A dermoscopic photograph of a skin lesion.
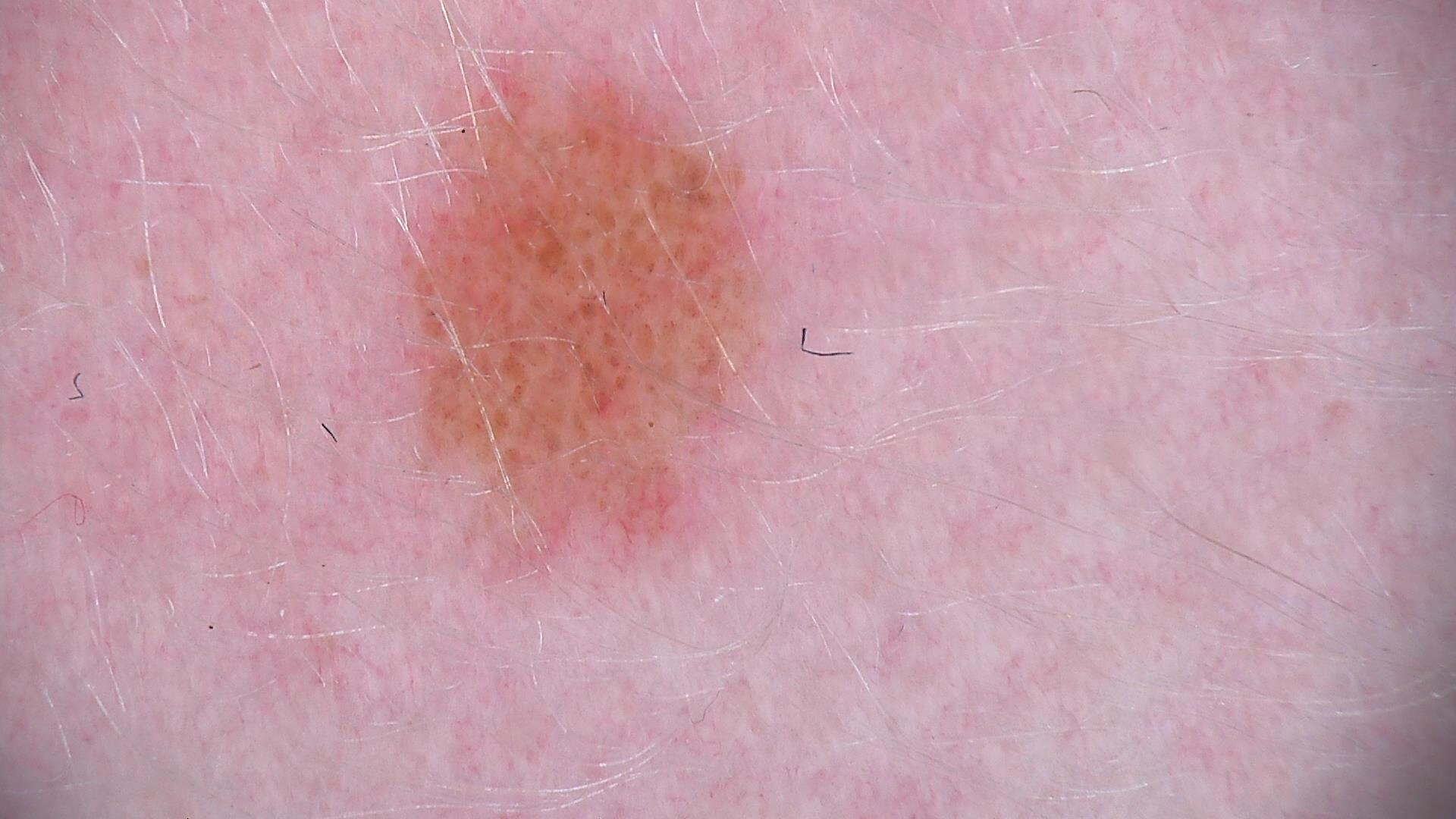Conclusion: Diagnosed as a compound nevus.